The photo was captured at a distance, the patient is a female aged 40–49, the back of the hand is involved.
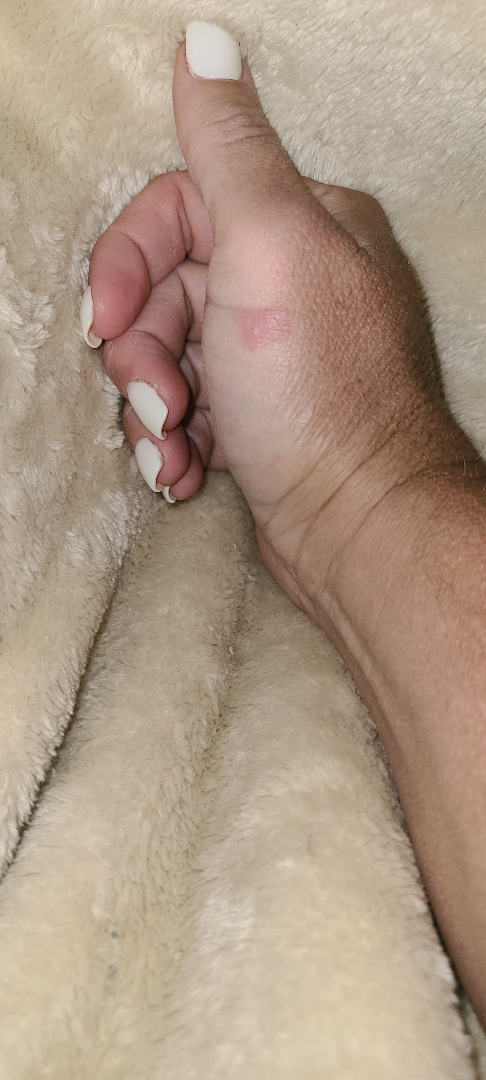reported symptoms=burning and bothersome appearance
patient's own categorization=a rash
texture=raised or bumpy
present for=less than one week
other reported symptoms=fatigue, fever, chills and joint pain
assessment=most consistent with Contact dermatitis; less probable is Eczema; a remote consideration is Burn erythema of back of hand; less likely is Acute dermatitis, NOS; lower on the differential is Phytophotodermatitis; a more distant consideration is Irritant Contact Dermatitis